The photograph was taken at a distance: 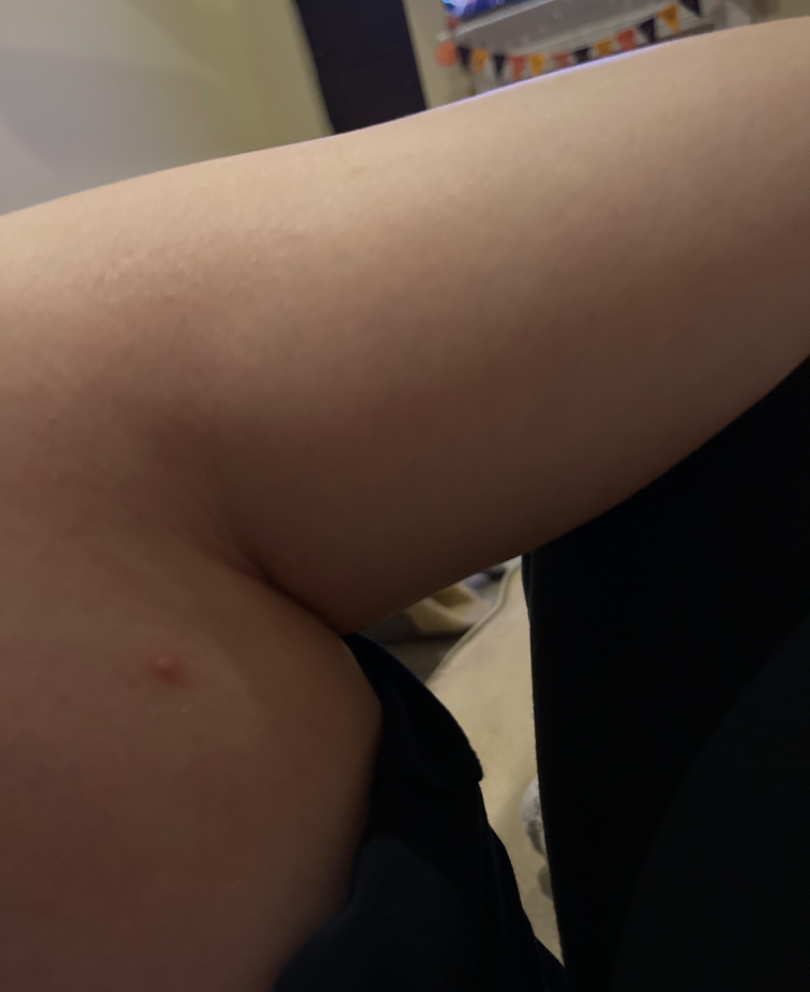Findings:
• assessment: indeterminate